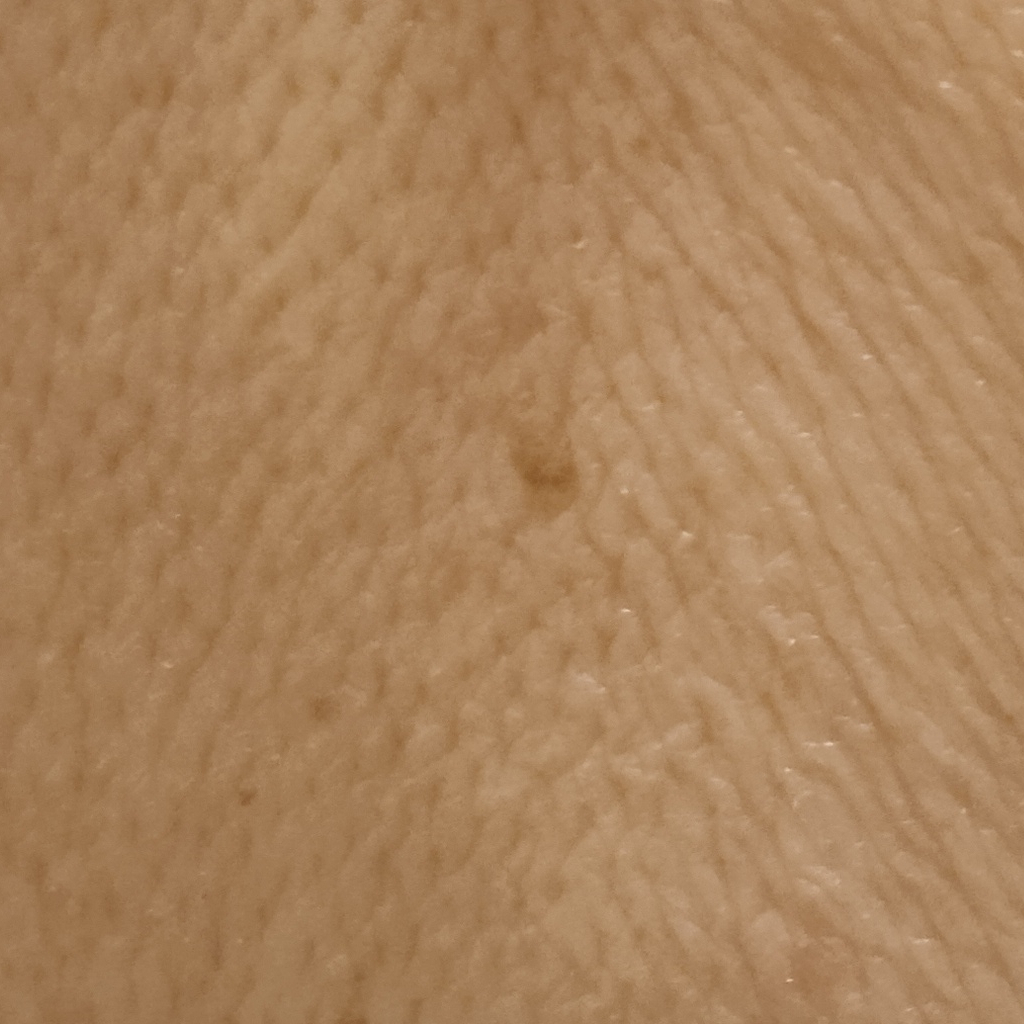Findings:
A female patient aged 71. Few moles overall by the patient's own estimate. Collected as part of a research study, without a referral diagnosis. The patient says their skin reddens with sun exposure. On a questionnaire the patient reported a personal history of cancer and a personal history of skin cancer. A clinical photograph of a skin lesion. Located on the back. Measuring roughly 3.8 mm.
Conclusion:
The consensus diagnosis for this lesion was a seborrheic keratosis.